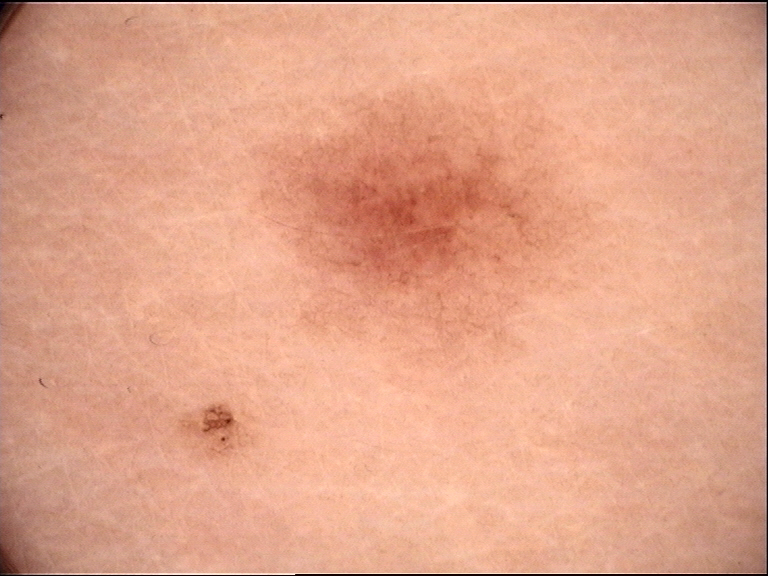Impression:
Consistent with a dysplastic junctional nevus.